A dermoscopic close-up of a skin lesion.
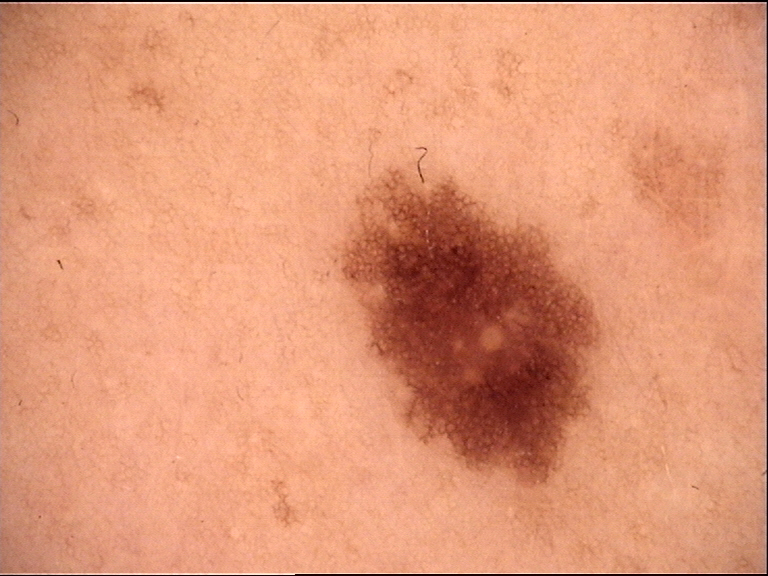Q: What is the diagnosis?
A: dysplastic junctional nevus (expert consensus)